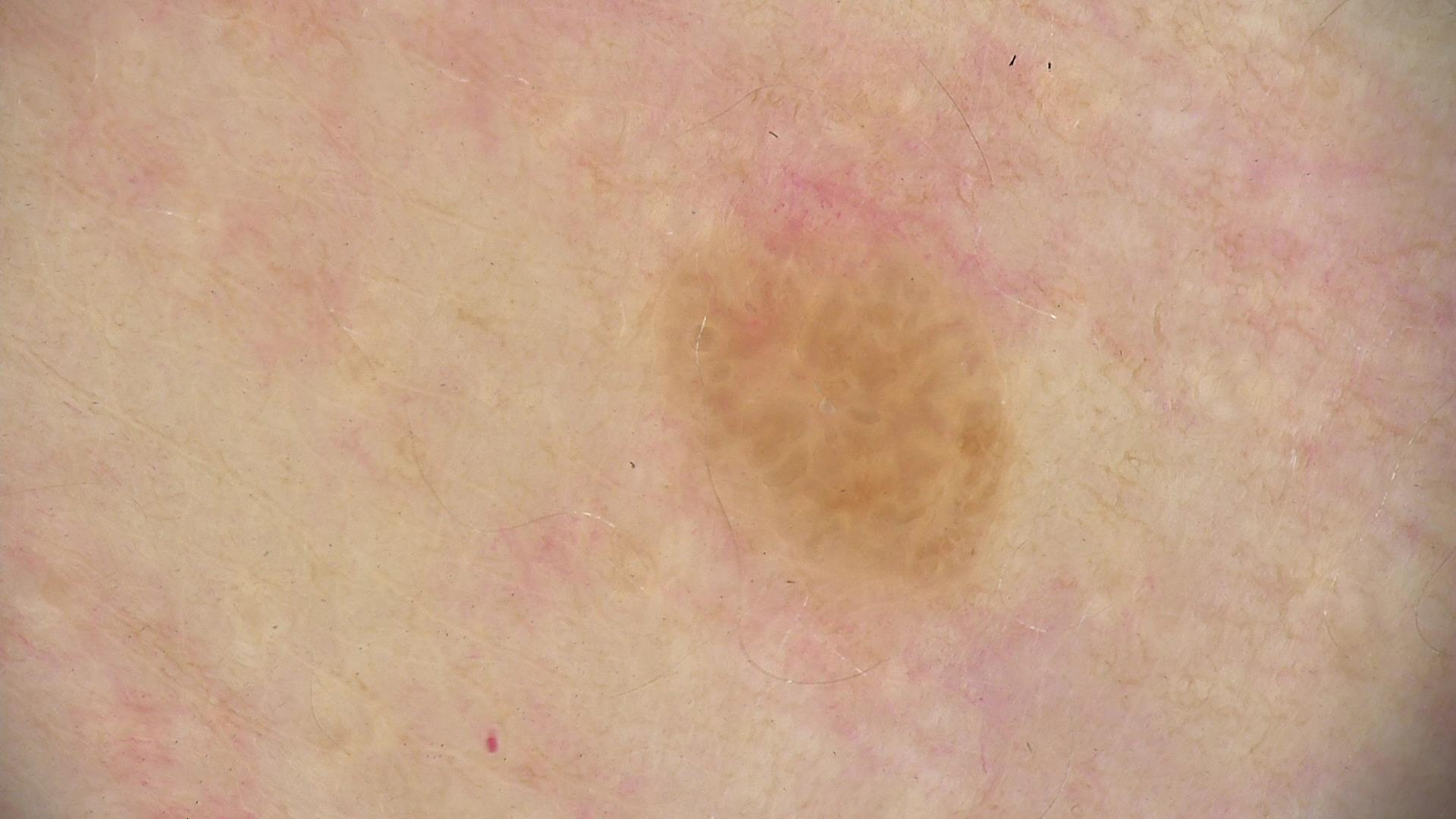Conclusion:
Consistent with a seborrheic keratosis.